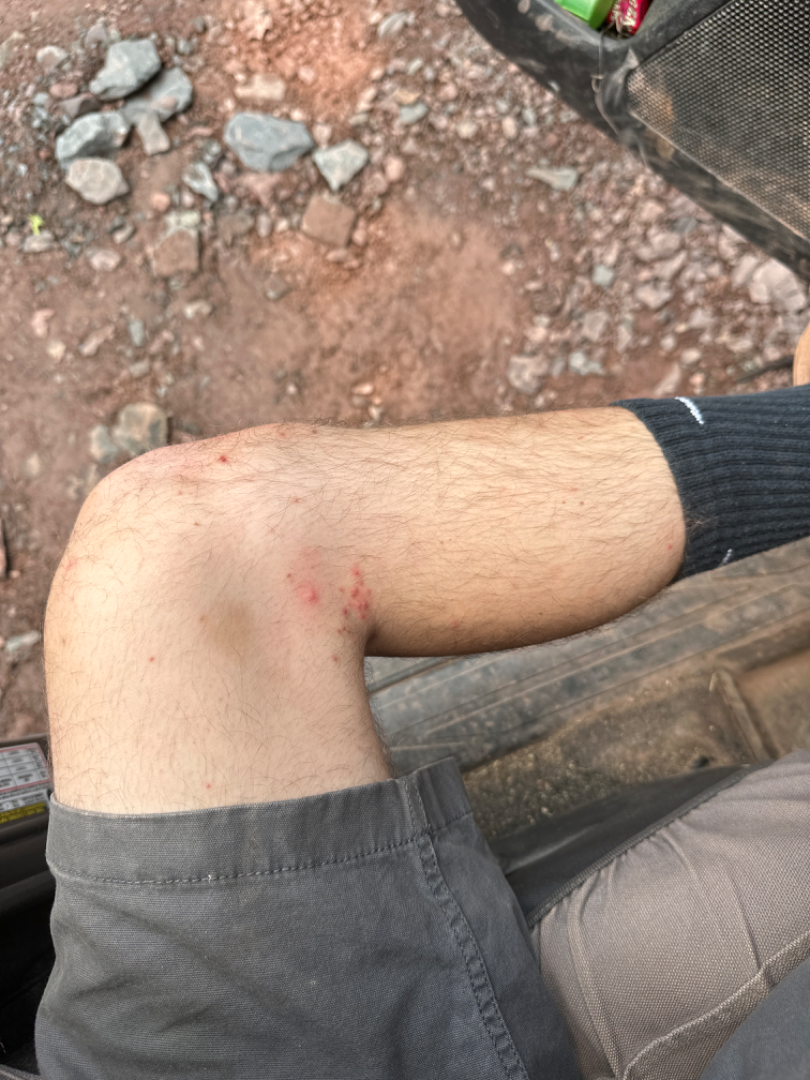assessment = indeterminate from the photograph, present for = about one day, skin tone = non-clinician graders estimated Monk skin tone scale 3, framing = at a distance, site = leg, patient describes the issue as = a rash, described texture = raised or bumpy, reported symptoms = bothersome appearance.